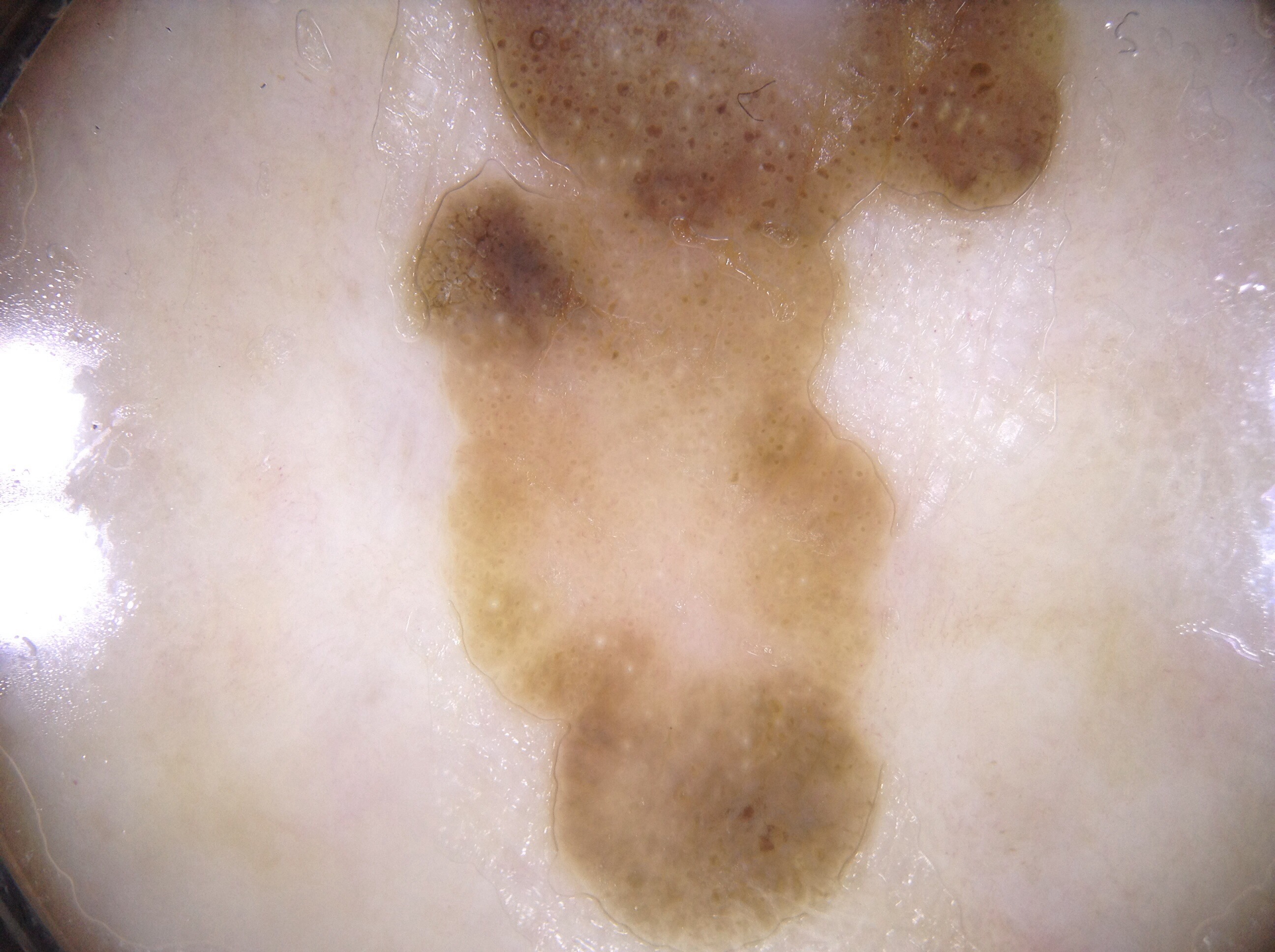{
  "patient": {
    "sex": "male",
    "age_approx": "85+"
  },
  "image": {
    "modality": "dermoscopy"
  },
  "lesion_location": {
    "bbox_xyxy": [
      399,
      0,
      1065,
      937
    ]
  },
  "dermoscopic_features": {
    "present": [
      "milia-like cysts"
    ],
    "absent": [
      "negative network",
      "streaks",
      "pigment network"
    ]
  },
  "diagnosis": {
    "name": "seborrheic keratosis",
    "malignancy": "benign",
    "lineage": "keratinocytic",
    "provenance": "clinical"
  }
}